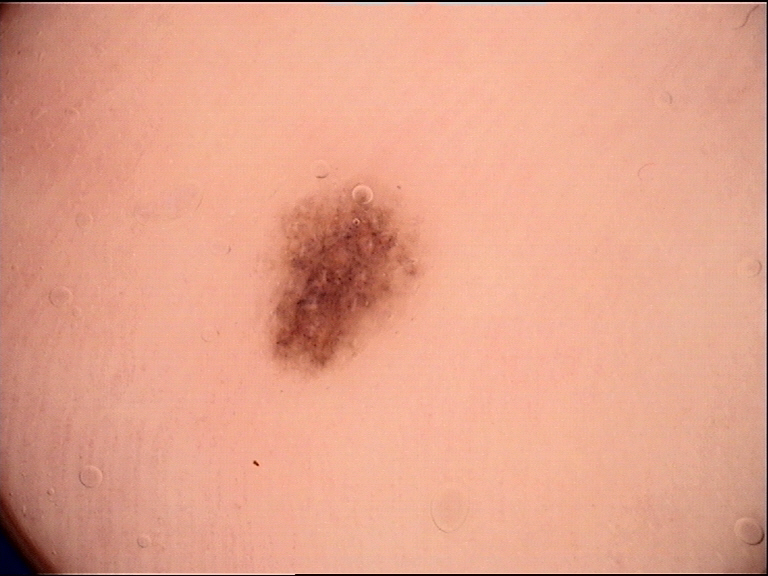Case:
– label · acral dysplastic junctional nevus (expert consensus)